A dermoscopy image of a single skin lesion.
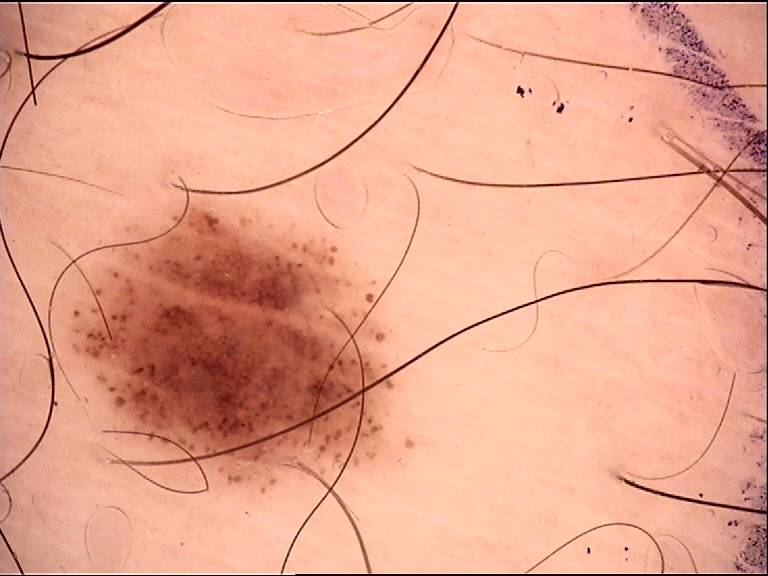| feature | finding |
|---|---|
| diagnostic label | dysplastic junctional nevus (expert consensus) |